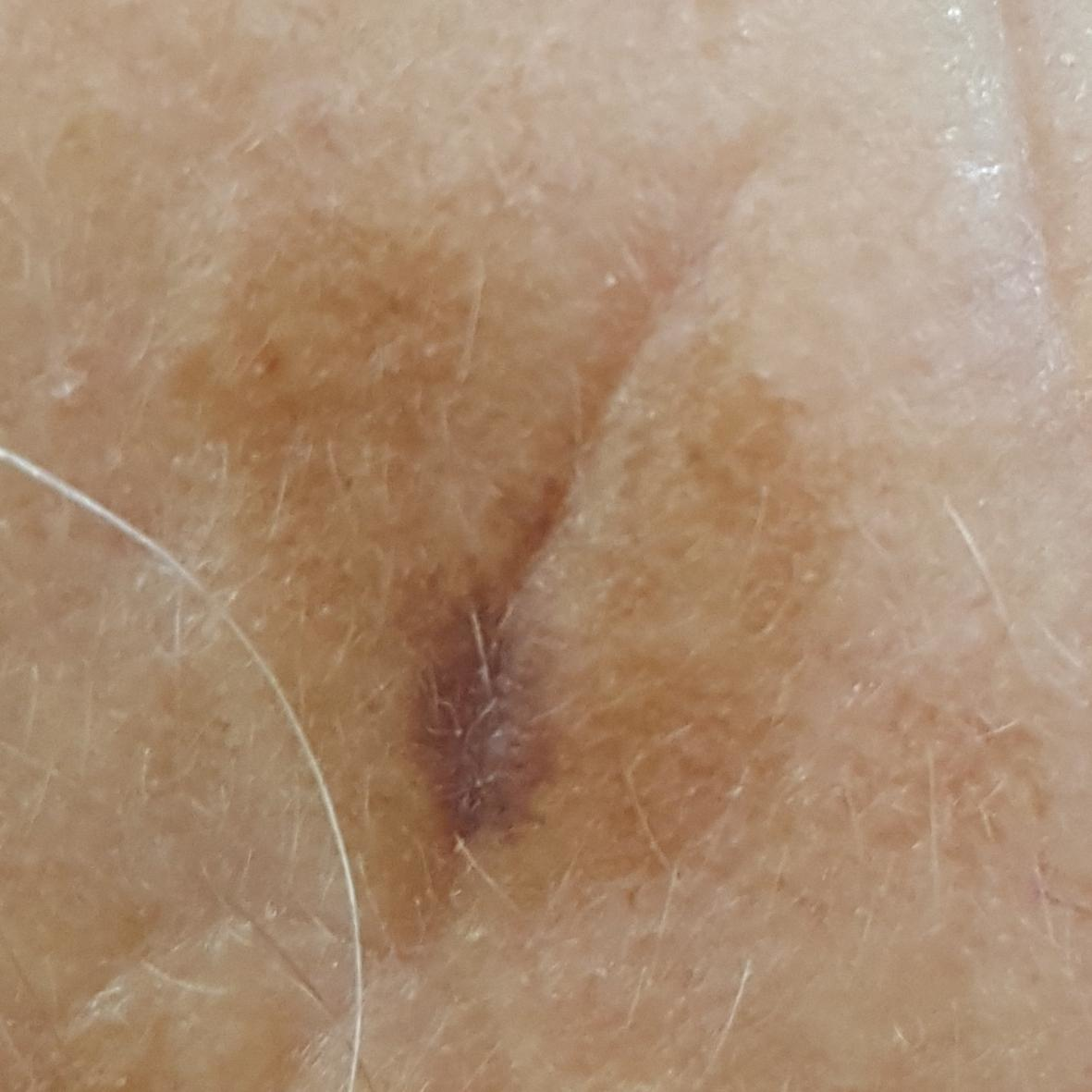impression=seborrheic keratosis (clinical consensus)